This is a close-up image — 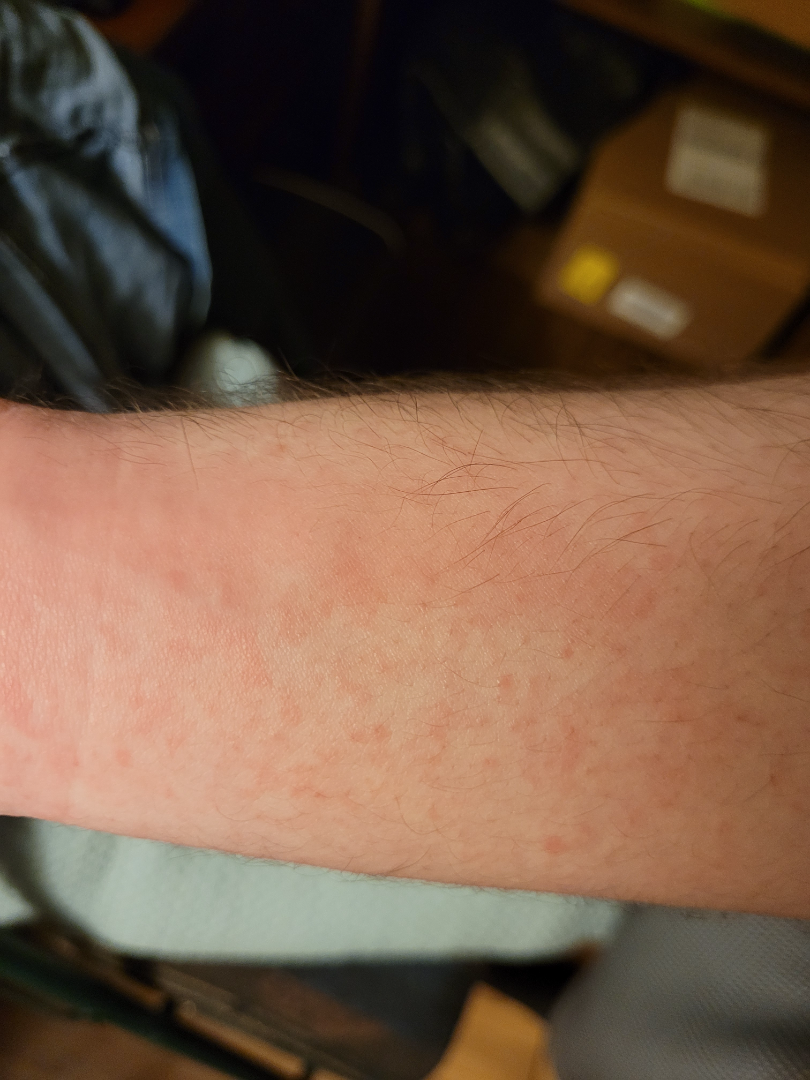| key | value |
|---|---|
| assessment | unable to determine |
| skin tone | non-clinician graders estimated a Monk Skin Tone of 2 |